An image taken at an angle.
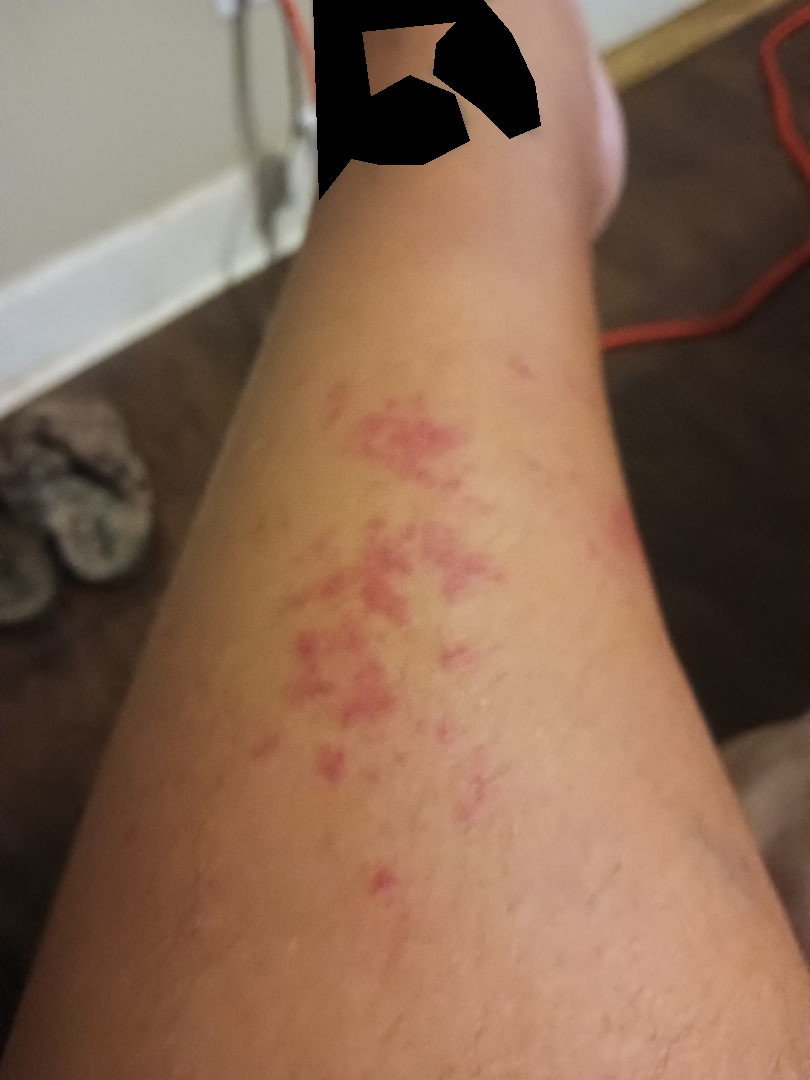Purpura and Hemangioma were each considered, in no particular order; less likely is Vasculitis of the skin.